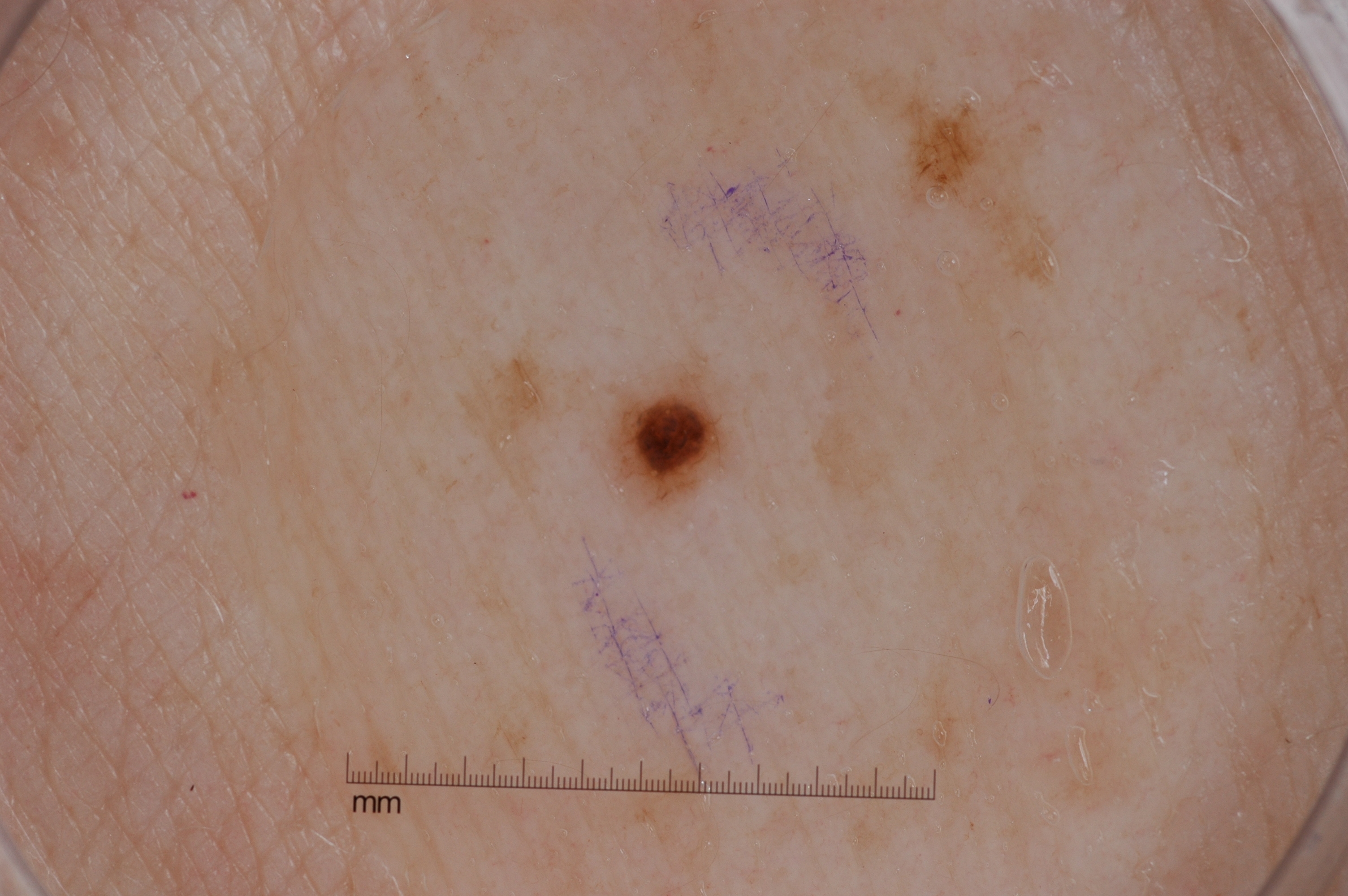Findings:
A dermoscopy image of a single skin lesion. With coordinates (x1, y1, x2, y2), the lesion spans (597, 347, 740, 516).
Impression:
Consistent with a melanocytic nevus.